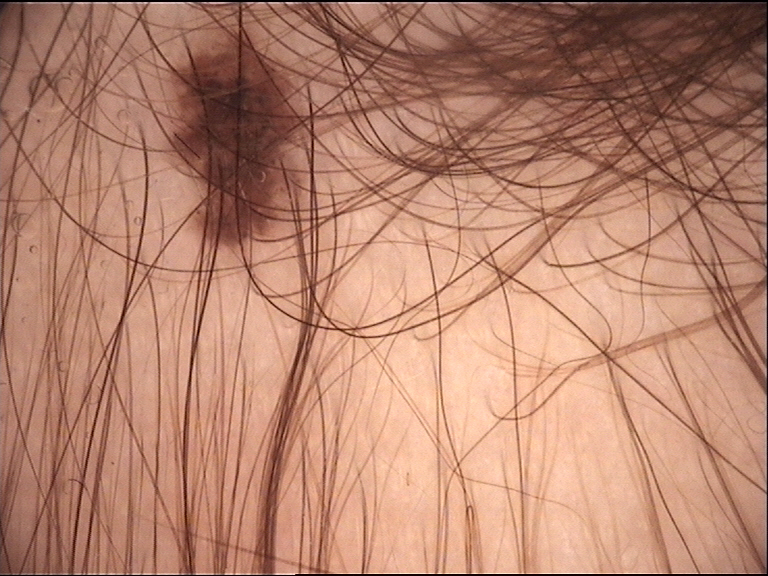A dermoscopy image of a single skin lesion.
The architecture is that of a banal lesion.
Classified as a congenital junctional nevus.